A dermoscopy image of a single skin lesion: 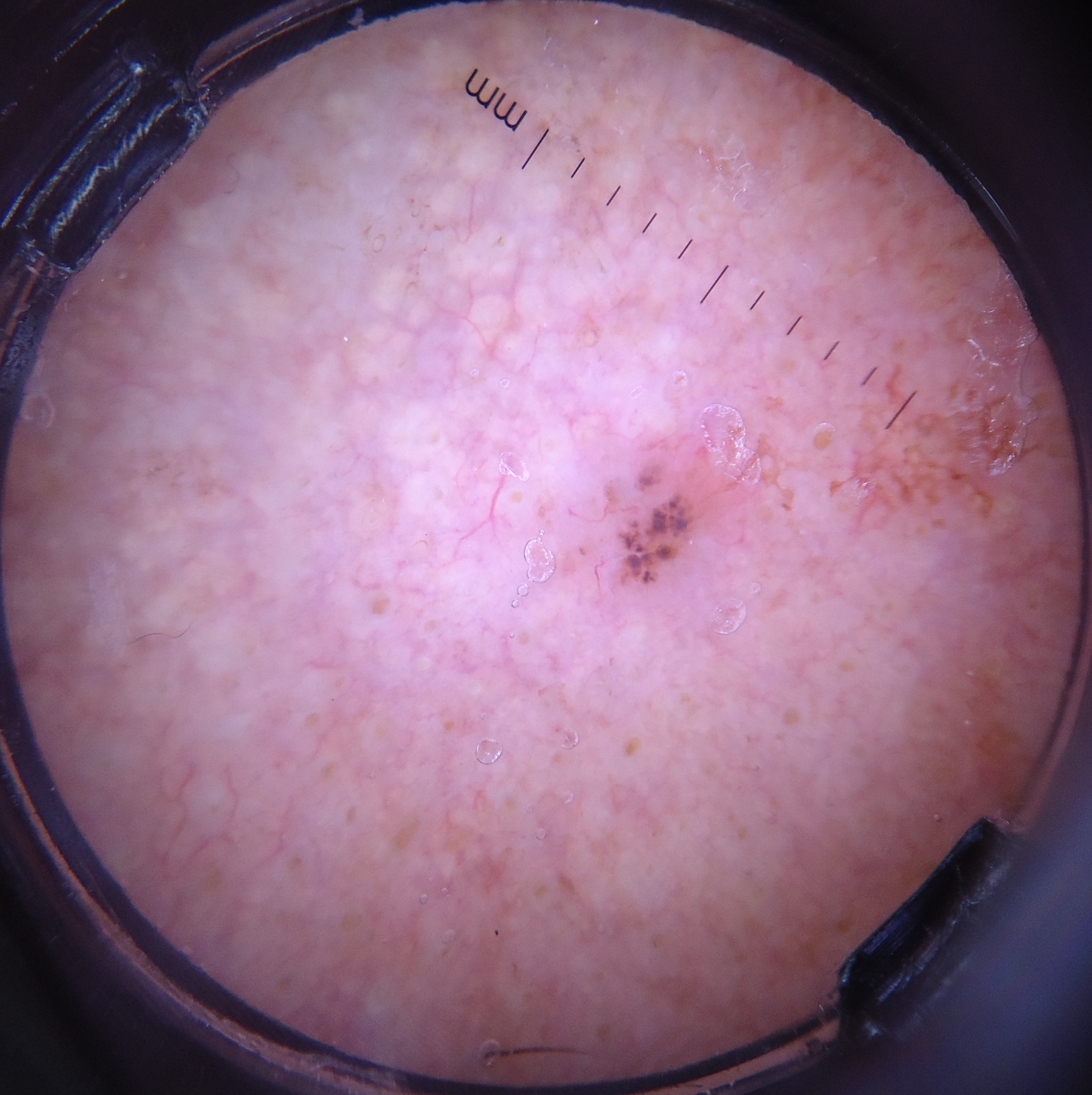The morphology is that of a keratinocytic lesion. Histopathology confirmed a basal cell carcinoma.